On a questionnaire the patient reported a history of sunbed use. A moderate number of moles by the patient's own estimate. A female patient age 47. A skin lesion imaged with a dermatoscope. Collected as part of a research study, without a referral diagnosis. The patient says their skin tans without first burning.
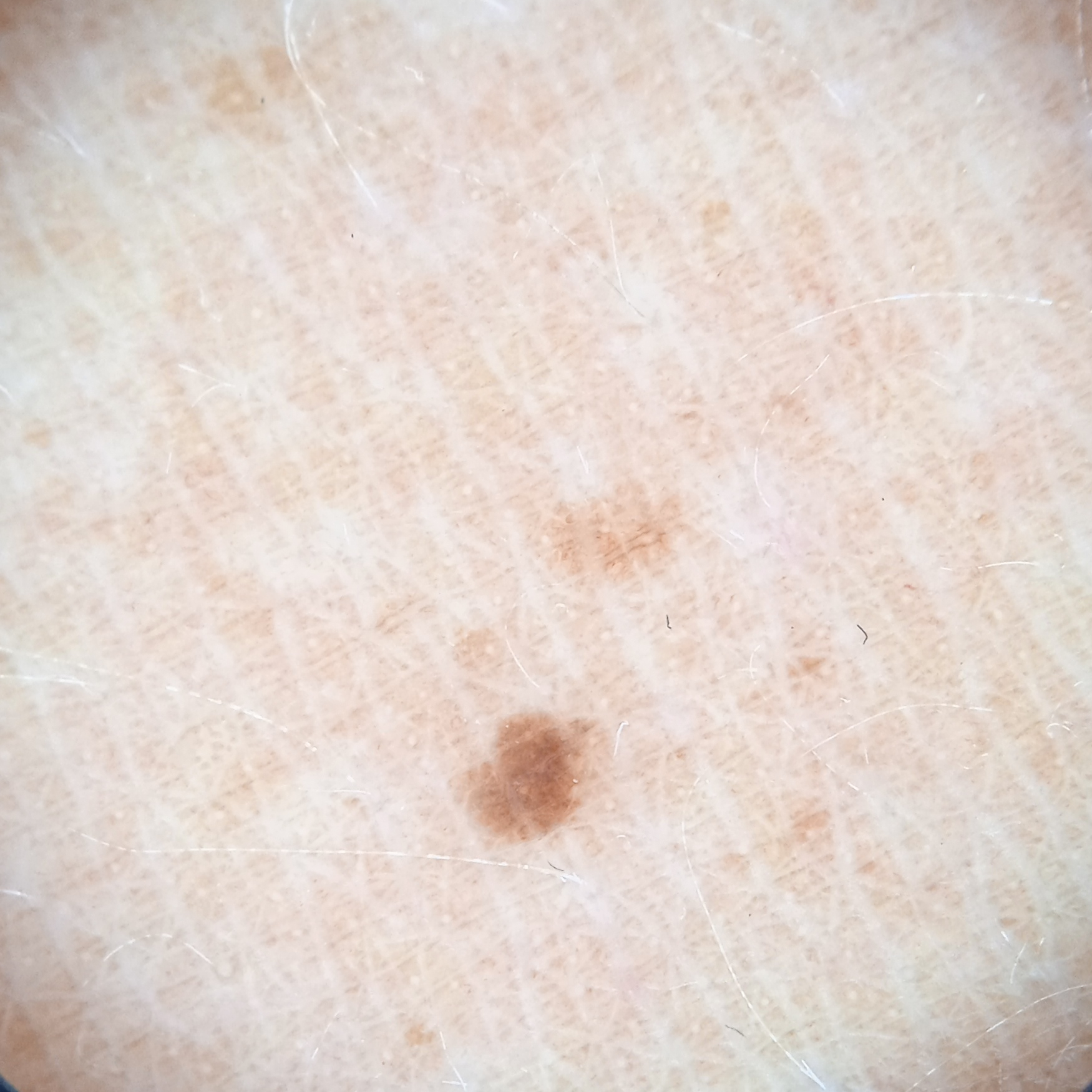<case>
<lesion_location>the back</lesion_location>
<lesion_size>
<diameter_mm>1.8</diameter_mm>
</lesion_size>
<diagnosis>
<name>melanocytic nevus</name>
<malignancy>benign</malignancy>
</diagnosis>
</case>